Recorded as Fitzpatrick skin type II · a dermatoscopic image of a skin lesion · a female subject in their mid- to late 30s.
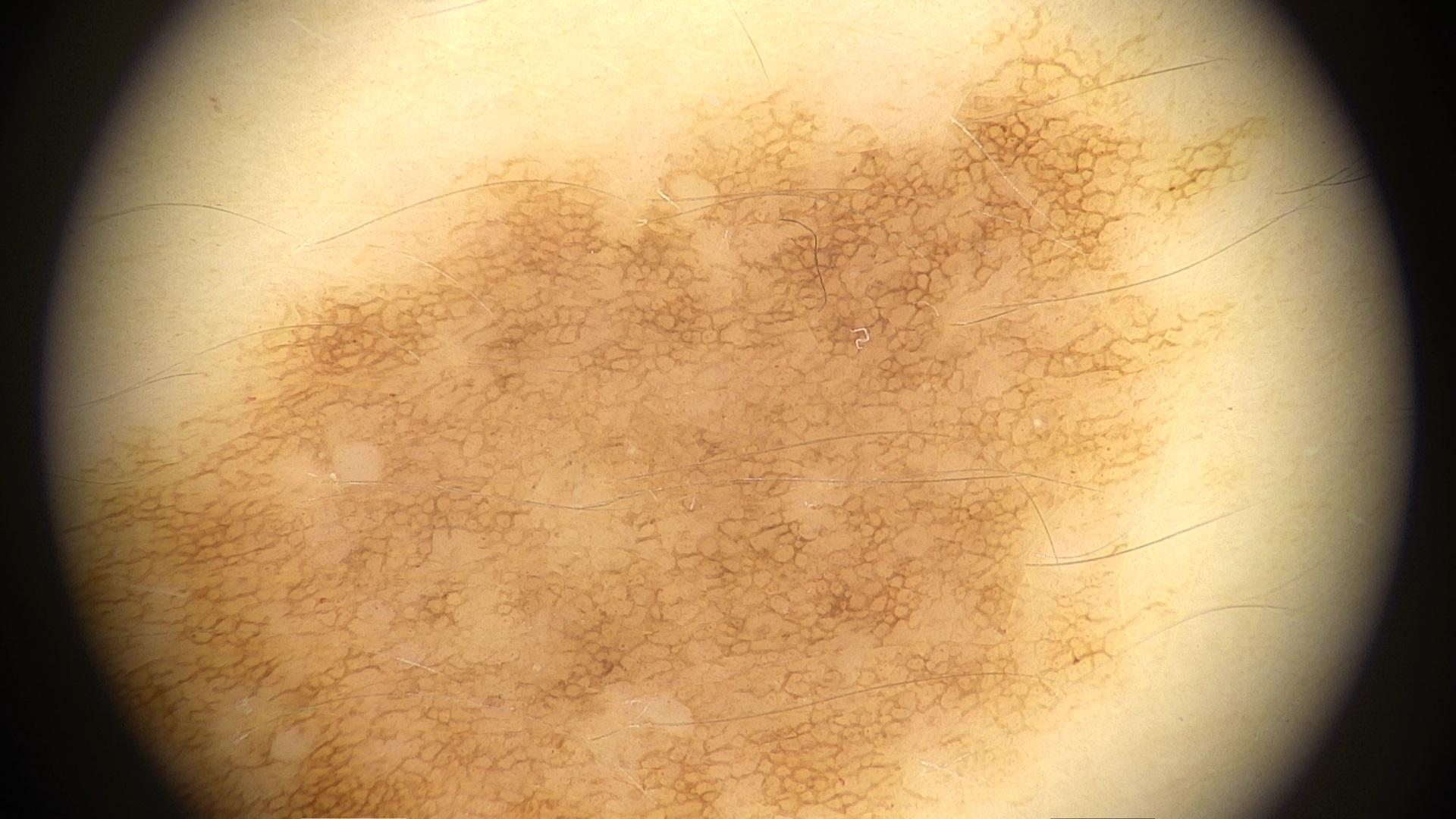The lesion is located on the posterior trunk.
Clinically diagnosed as a benign lesion — a nevus.